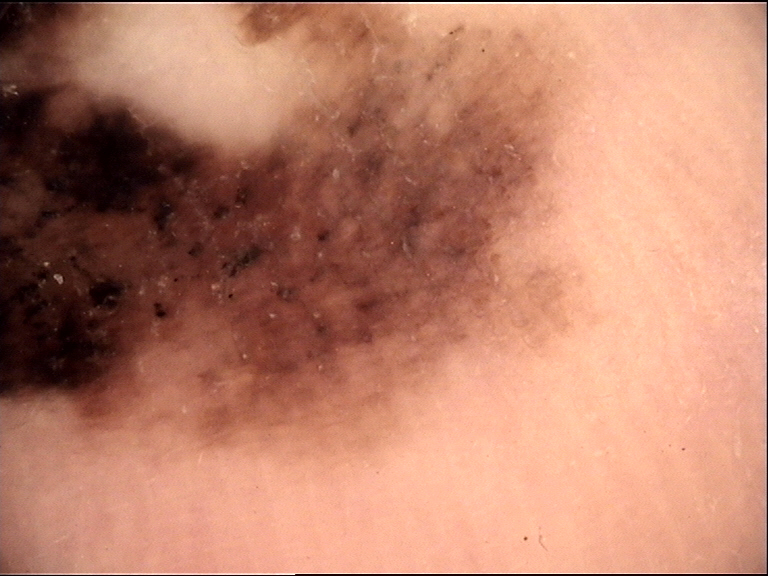pathology: acral lentiginous melanoma (biopsy-proven).